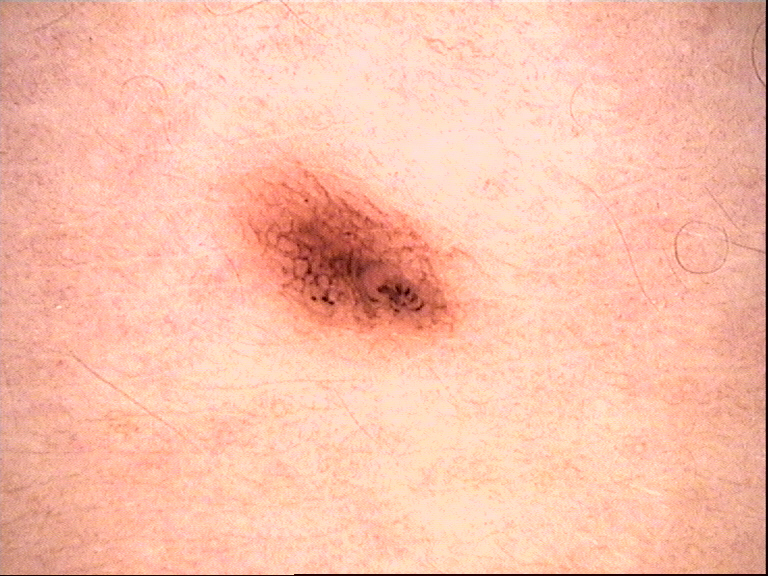Q: What was the diagnostic impression?
A: dysplastic junctional nevus (expert consensus)